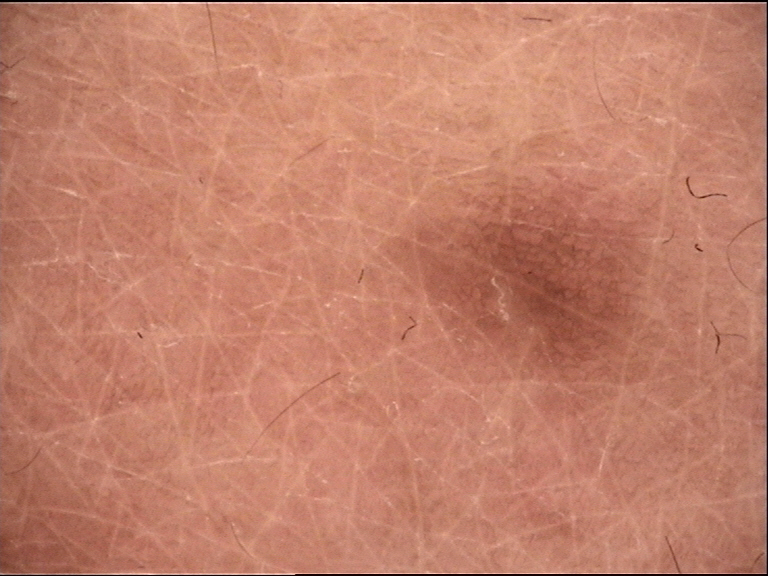A skin lesion imaged with a dermatoscope.
The architecture is that of a fibro-histiocytic lesion.
Diagnosed as a benign lesion — a dermatofibroma.